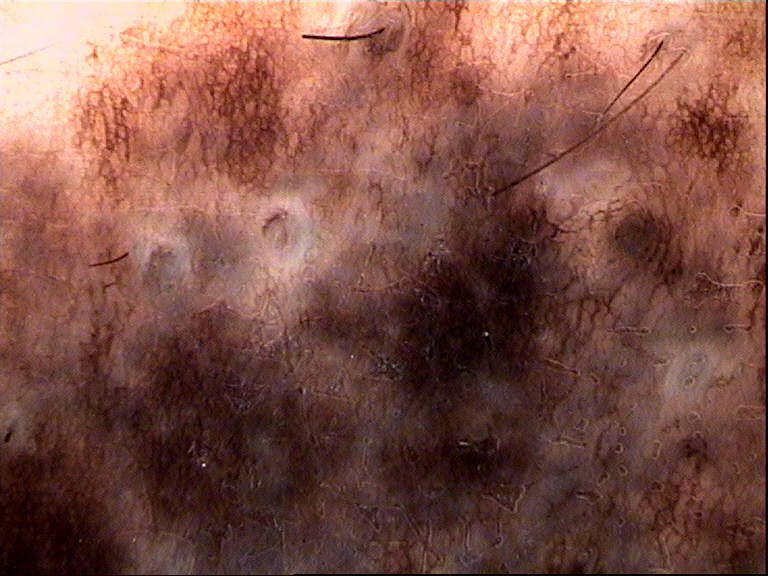Conclusion:
Consistent with a congenital compound nevus.